A dermoscopy image of a single skin lesion.
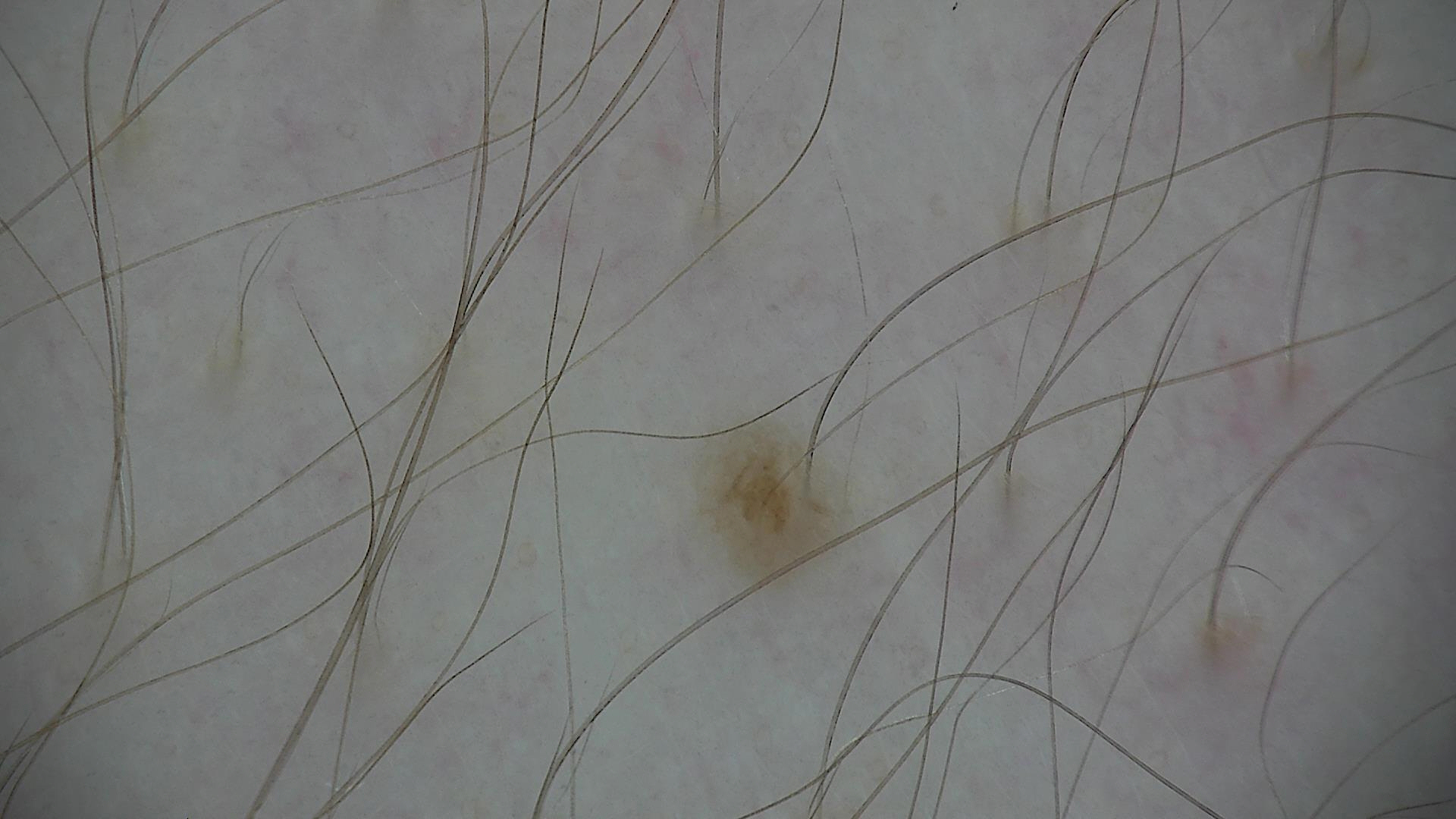Classified as a dysplastic junctional nevus.